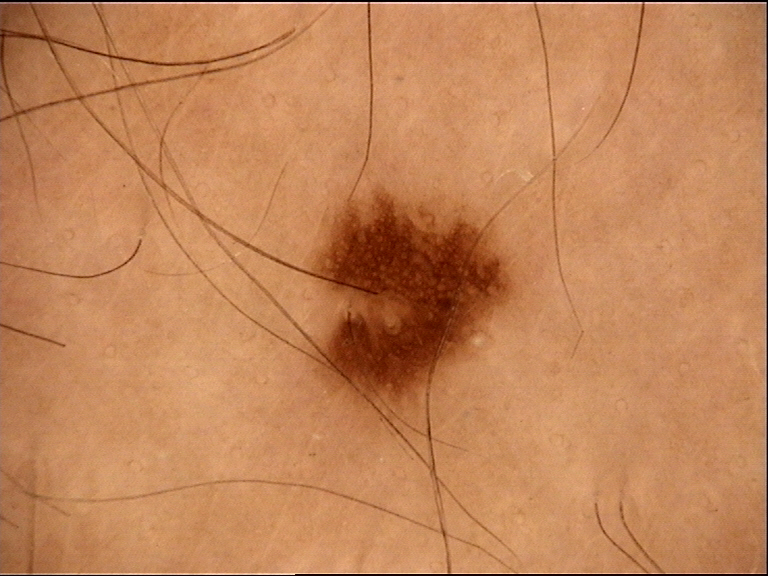The diagnostic label was a dysplastic junctional nevus.